The photograph was taken at a distance; the lesion involves the palm, back of the hand, top or side of the foot and sole of the foot; the subject is 18–29, female: 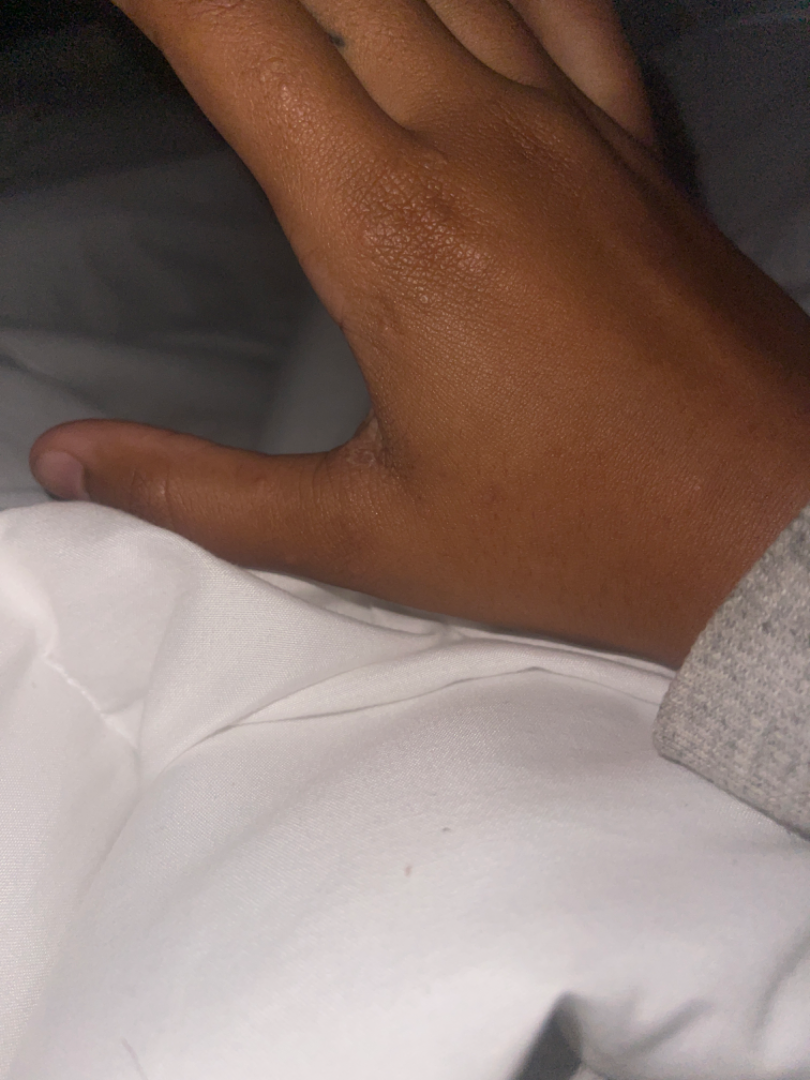<summary>
  <differential>
    <leading>Scabies</leading>
    <considered>Eczema</considered>
    <unlikely>Molluscum Contagiosum, Allergic Contact Dermatitis, Hypersensitivity</unlikely>
  </differential>
</summary>